The photo was captured at a distance; the lesion involves the back of the hand — 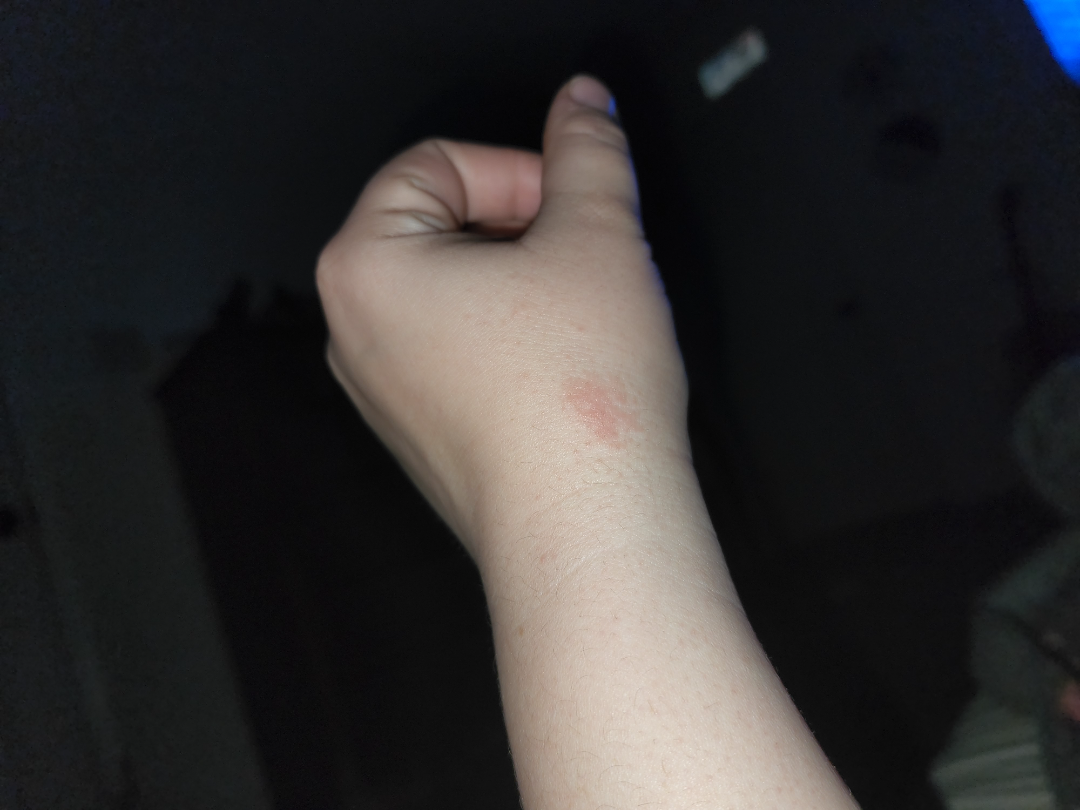skin tone: Fitzpatrick phototype I; lay reviewers estimated Monk skin tone scale 1 or 3 | history: less than one week | texture: raised or bumpy | patient-reported symptoms: itching | impression: the differential is split between Eczema and Allergic Contact Dermatitis.